The photograph is a close-up of the affected area — 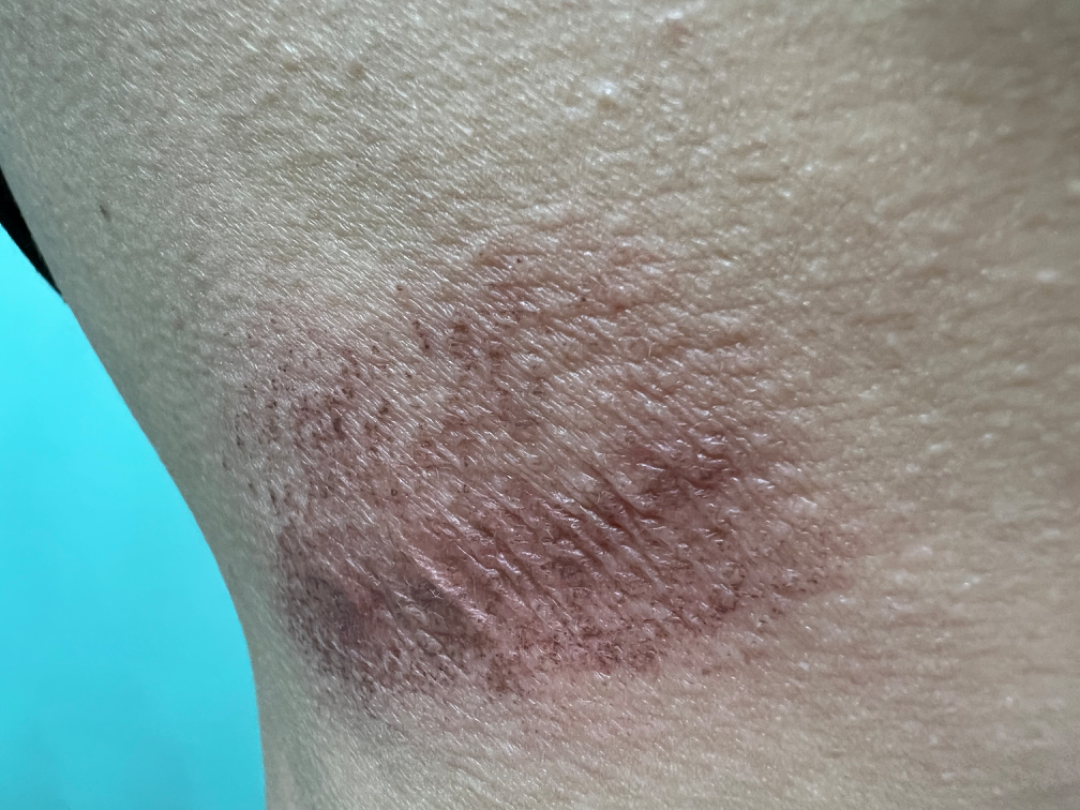The reviewing dermatologist was unable to assign a differential diagnosis from the image.